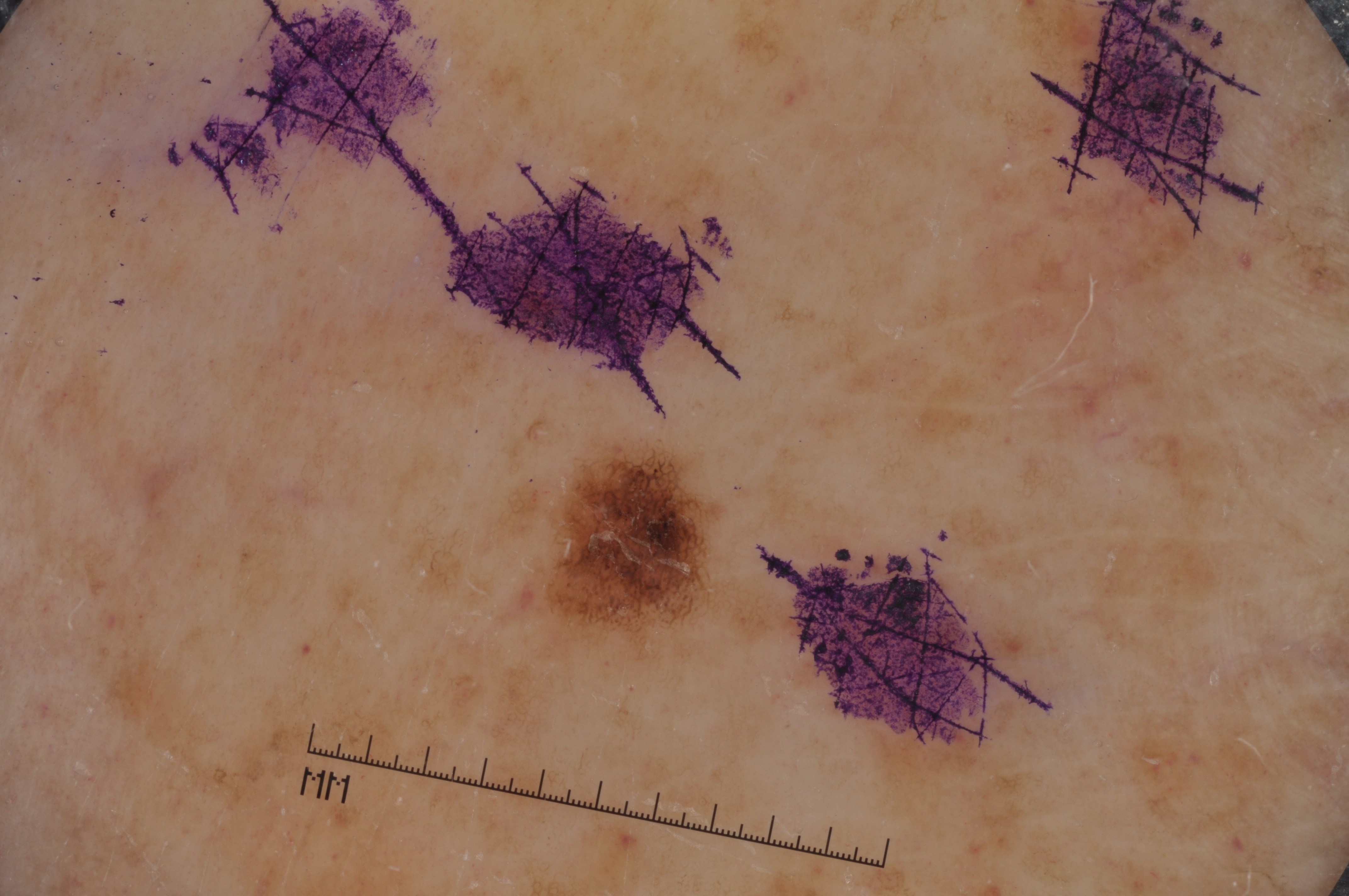modality = dermoscopy of a skin lesion; subject = male, about 75 years old; dermoscopic features = pigment network; location = (548, 455, 706, 630); extent = ~2% of the field; diagnostic label = a melanocytic nevus.